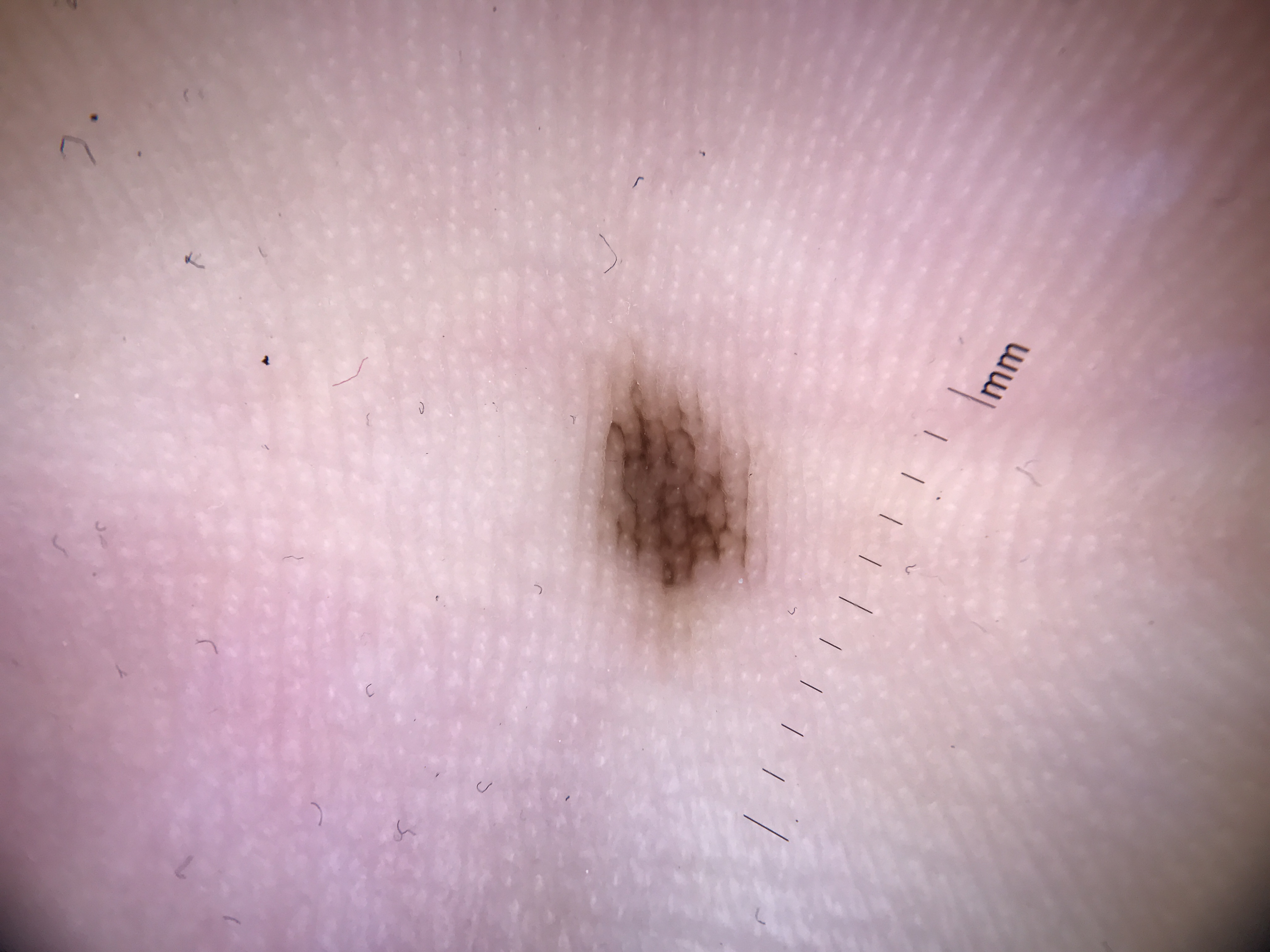| key | value |
|---|---|
| image type | dermatoscopy |
| lesion type | banal |
| class | acral junctional nevus (expert consensus) |